A skin lesion imaged with a dermatoscope.
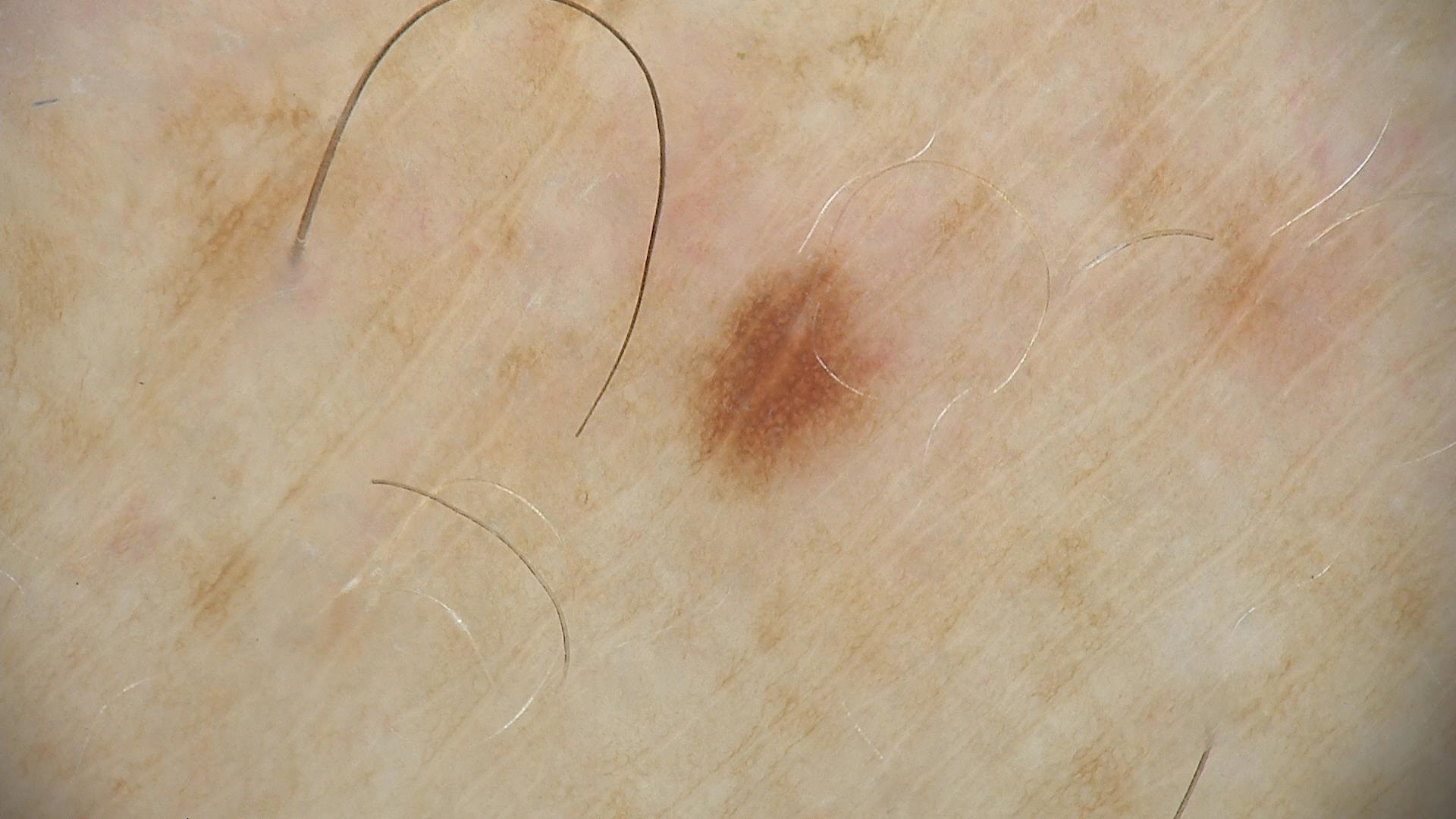diagnosis = dysplastic junctional nevus (expert consensus)